The photograph was taken at a distance. Female subject, age 30–39.
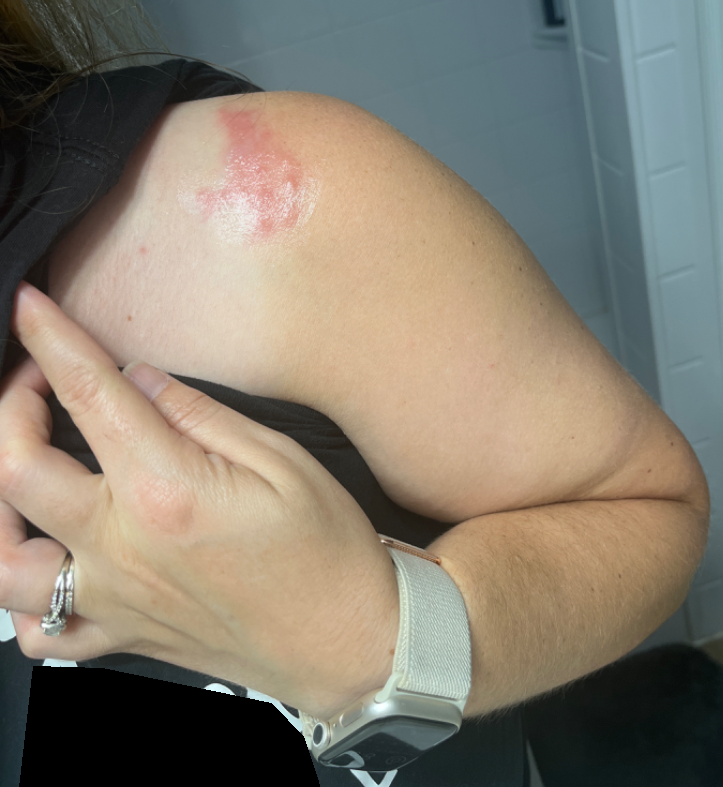Findings:
* patient-reported symptoms — bothersome appearance, pain and itching
* skin tone — Fitzpatrick skin type III; human graders estimated 3 on the Monk skin tone scale
* history — less than one week
* patient describes the issue as — a rash
* described texture — raised or bumpy
* impression — Allergic Contact Dermatitis (weight 0.54); Insect Bite (weight 0.23); Herpes Zoster (weight 0.23)